The patient is Fitzpatrick phototype II; a contact-polarized dermoscopy image of a skin lesion; a female patient aged 83 or older — 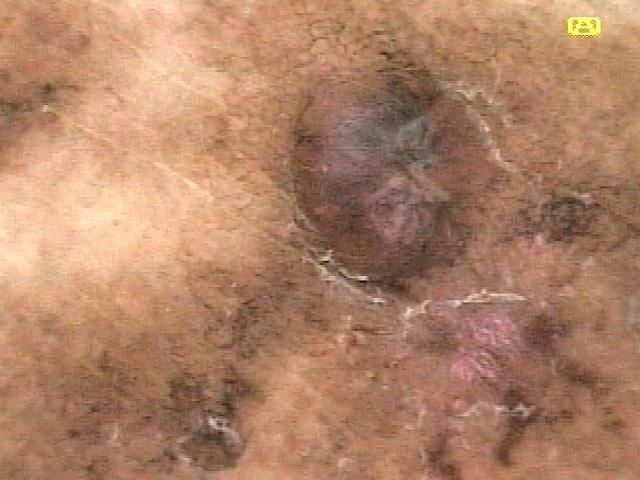Q: Where is the lesion located?
A: a lower extremity
Q: What is the diagnosis?
A: Melanoma (biopsy-proven)